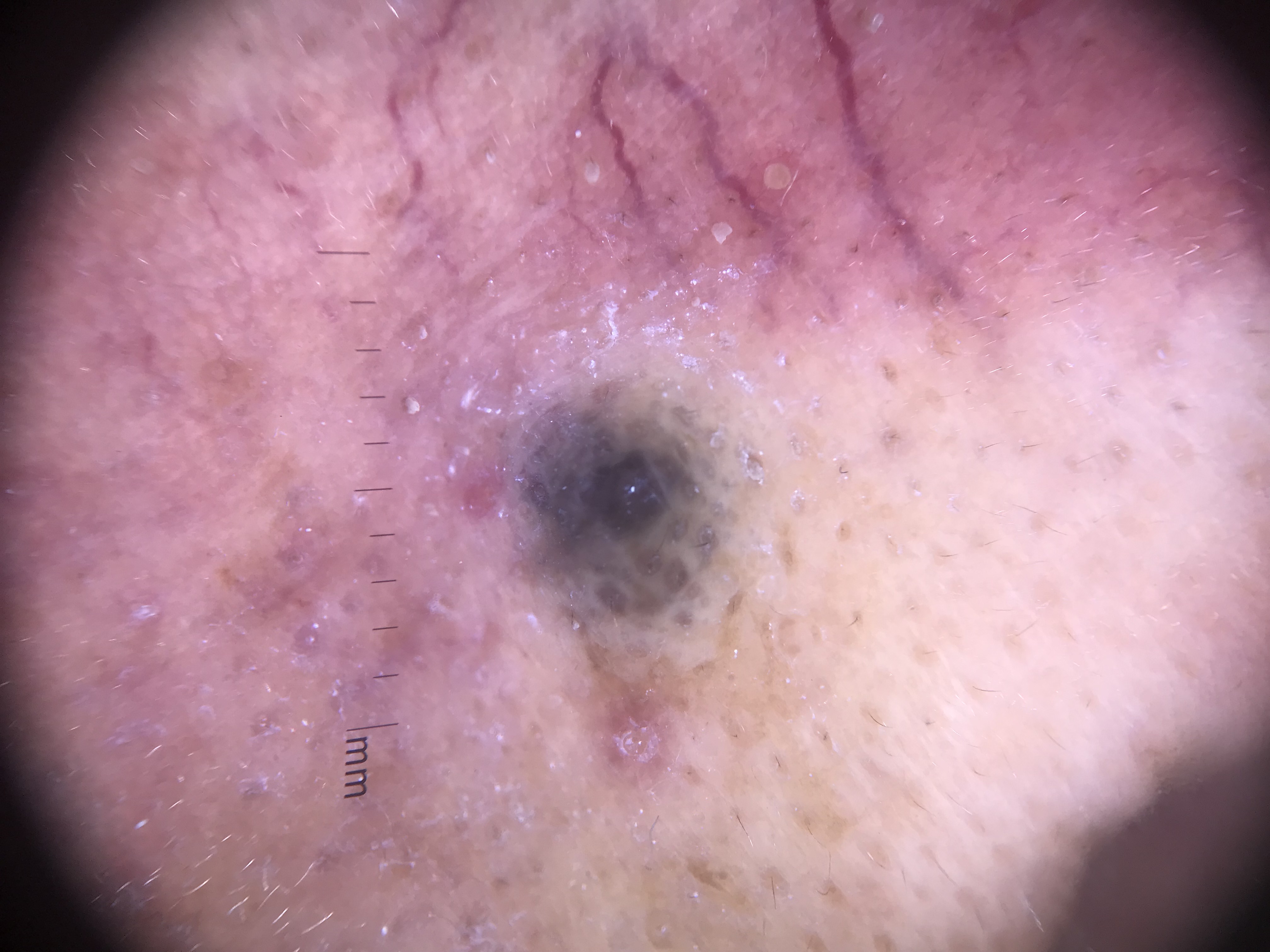A dermatoscopic image of a skin lesion. Labeled as a banal lesion — a blue nevus.